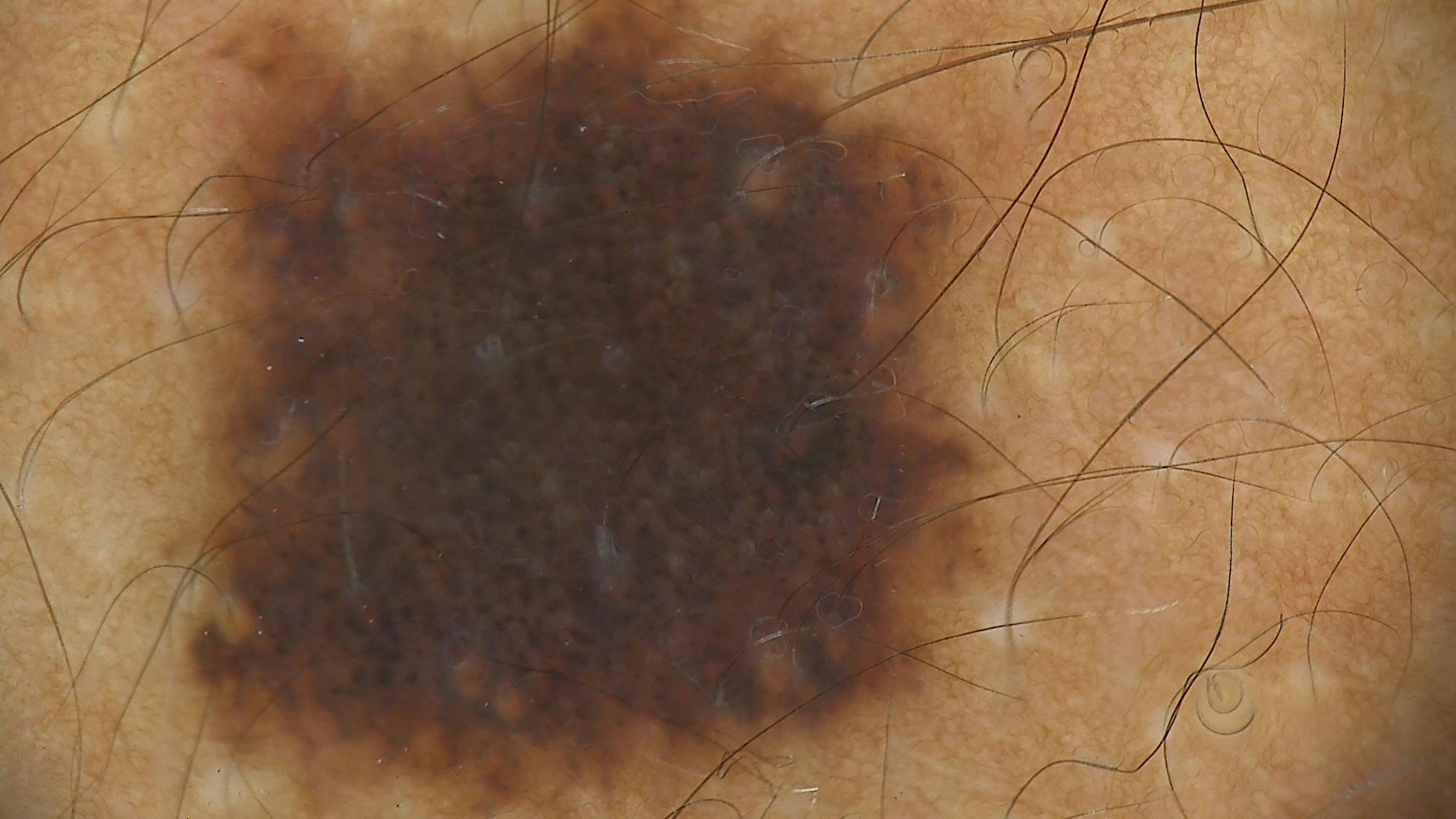A dermatoscopic image of a skin lesion. The diagnosis was a congenital dysplastic compound nevus.